Fitzpatrick phototype II; a male patient aged around 85 or older; a skin lesion imaged with contact-polarized dermoscopy: 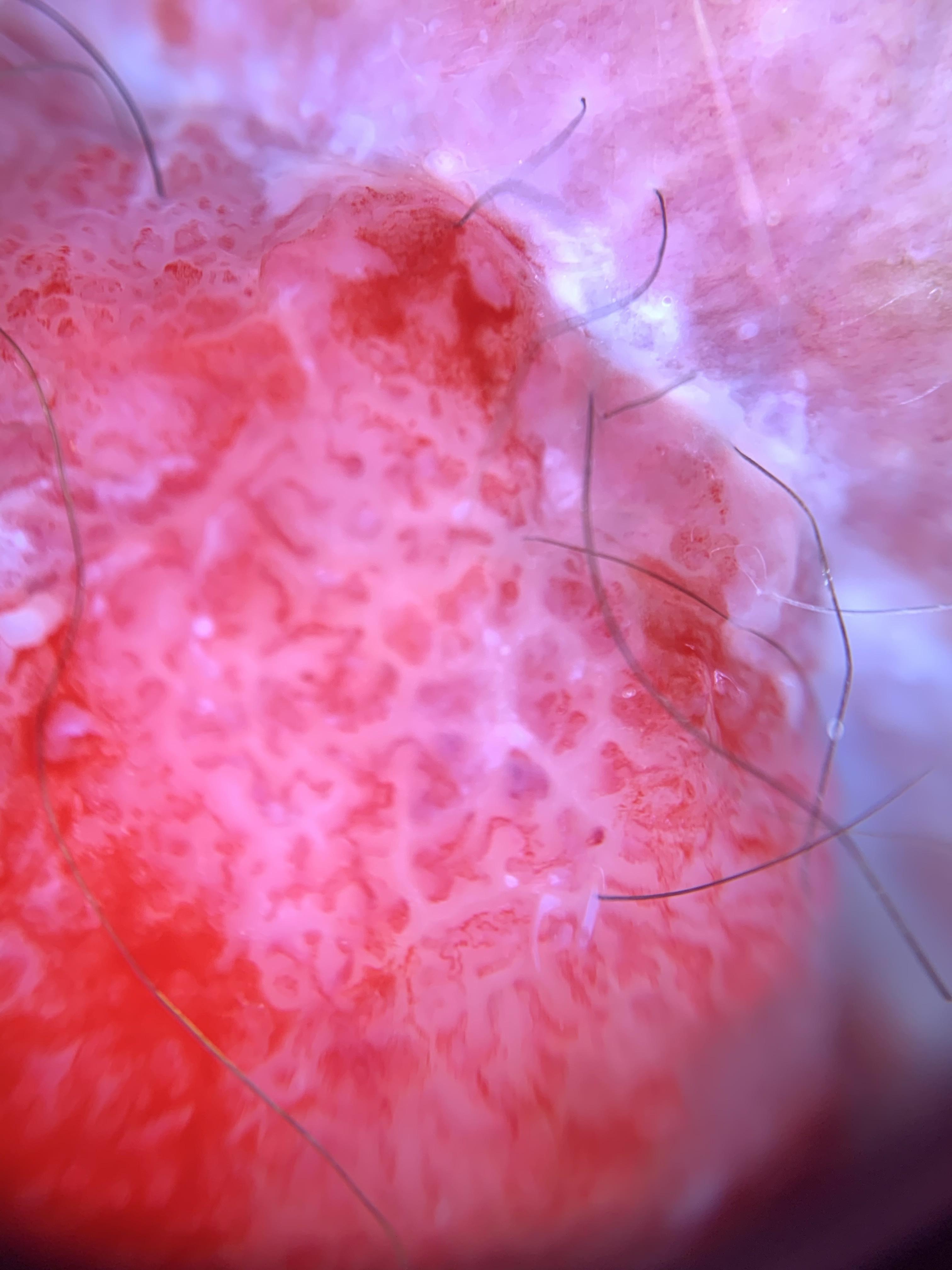Notes:
* body site · the trunk
* diagnostic label · Squamous cell carcinoma (biopsy-proven)